The photograph was taken at an angle — 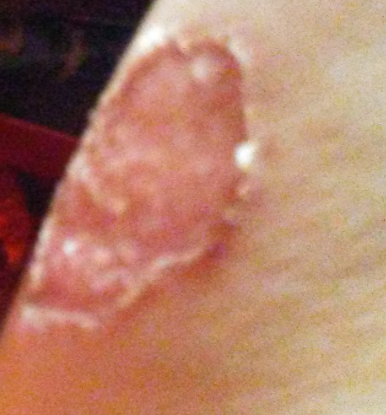Findings:
– dermatologist impression: most likely Ecthyma; also consider Porokeratosis; with consideration of Eczema